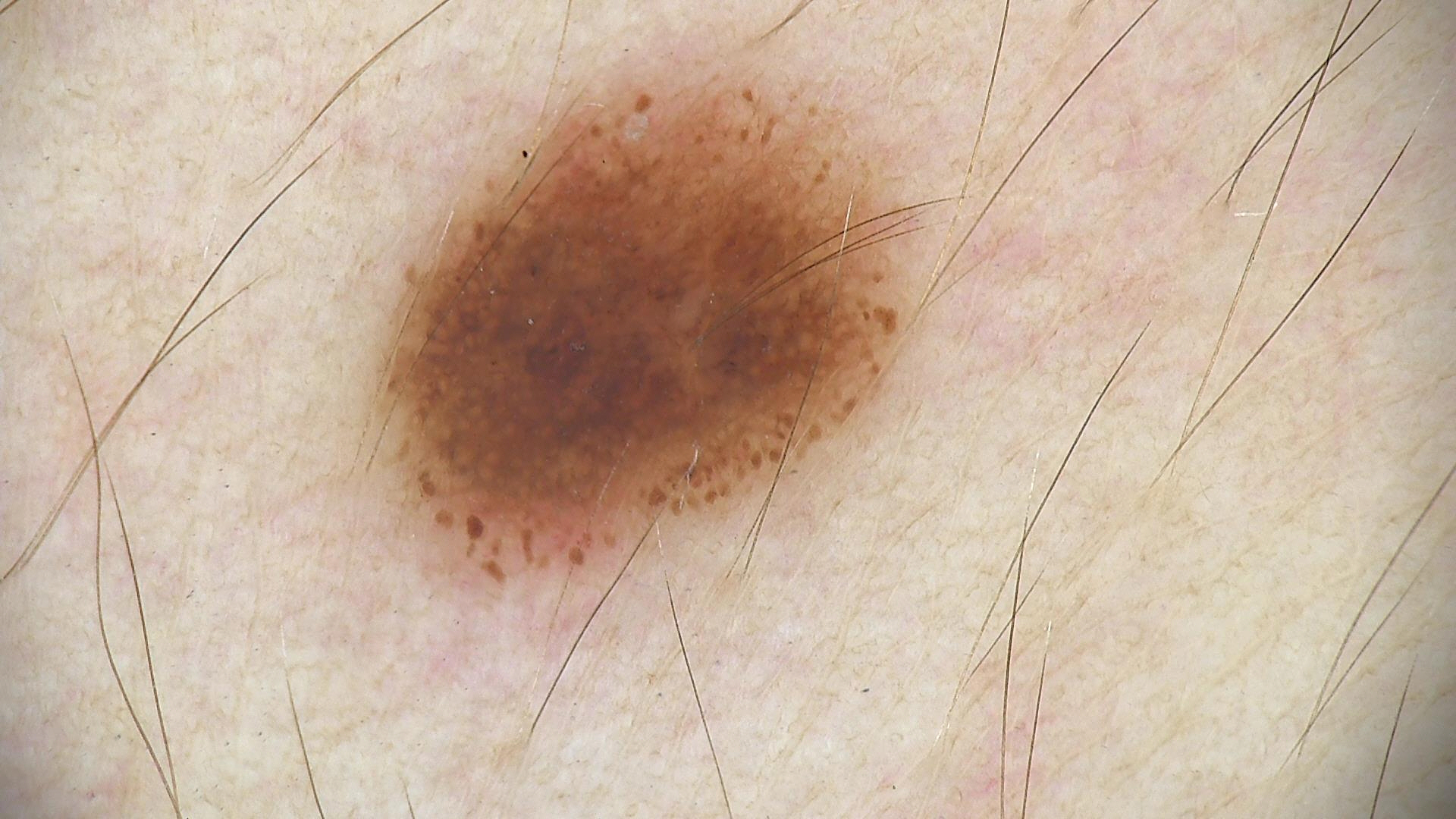modality: dermatoscopy | diagnosis: dysplastic junctional nevus (expert consensus).